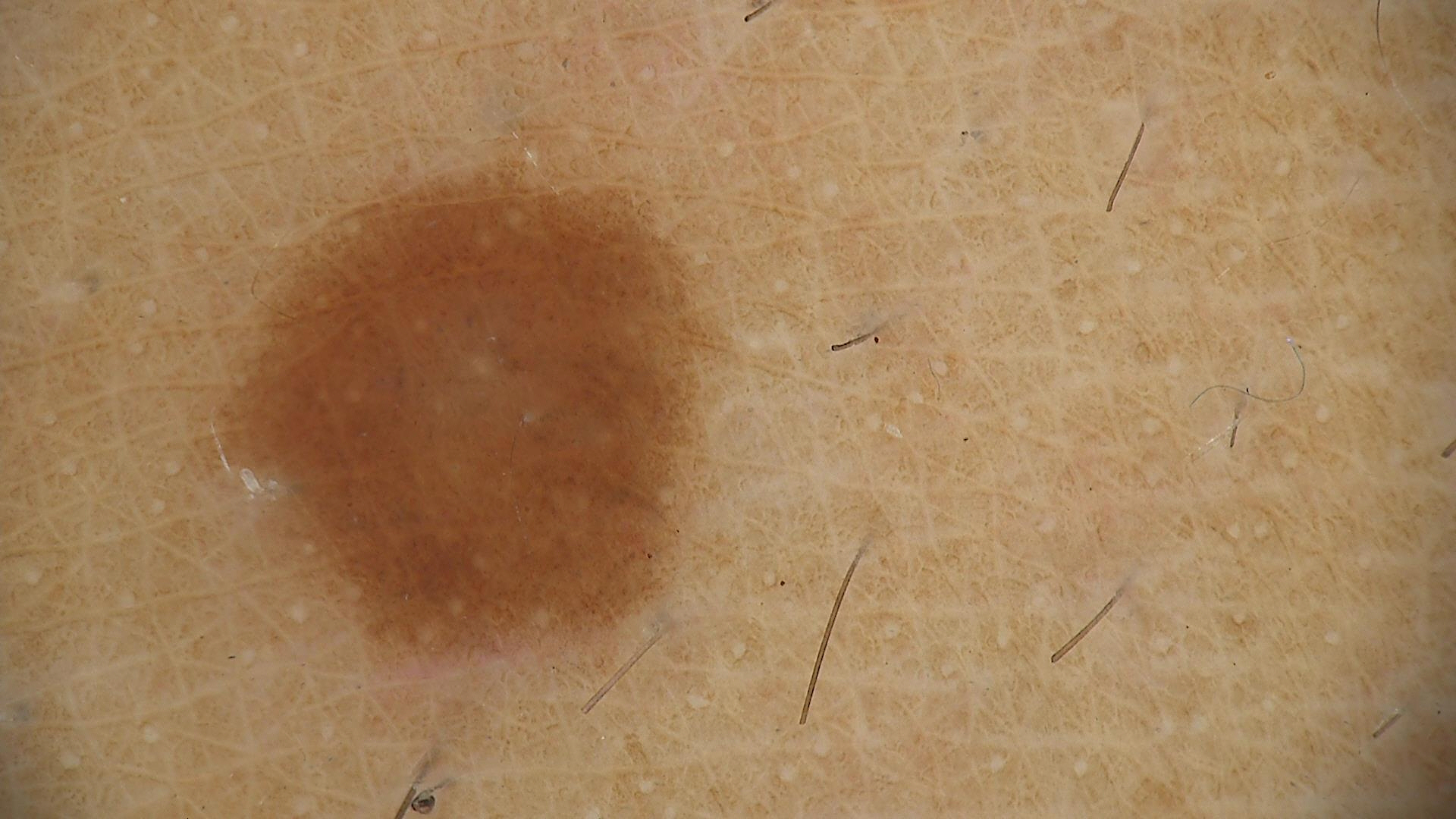The diagnosis was a benign lesion — a dysplastic junctional nevus.